A dermoscopic photograph of a skin lesion.
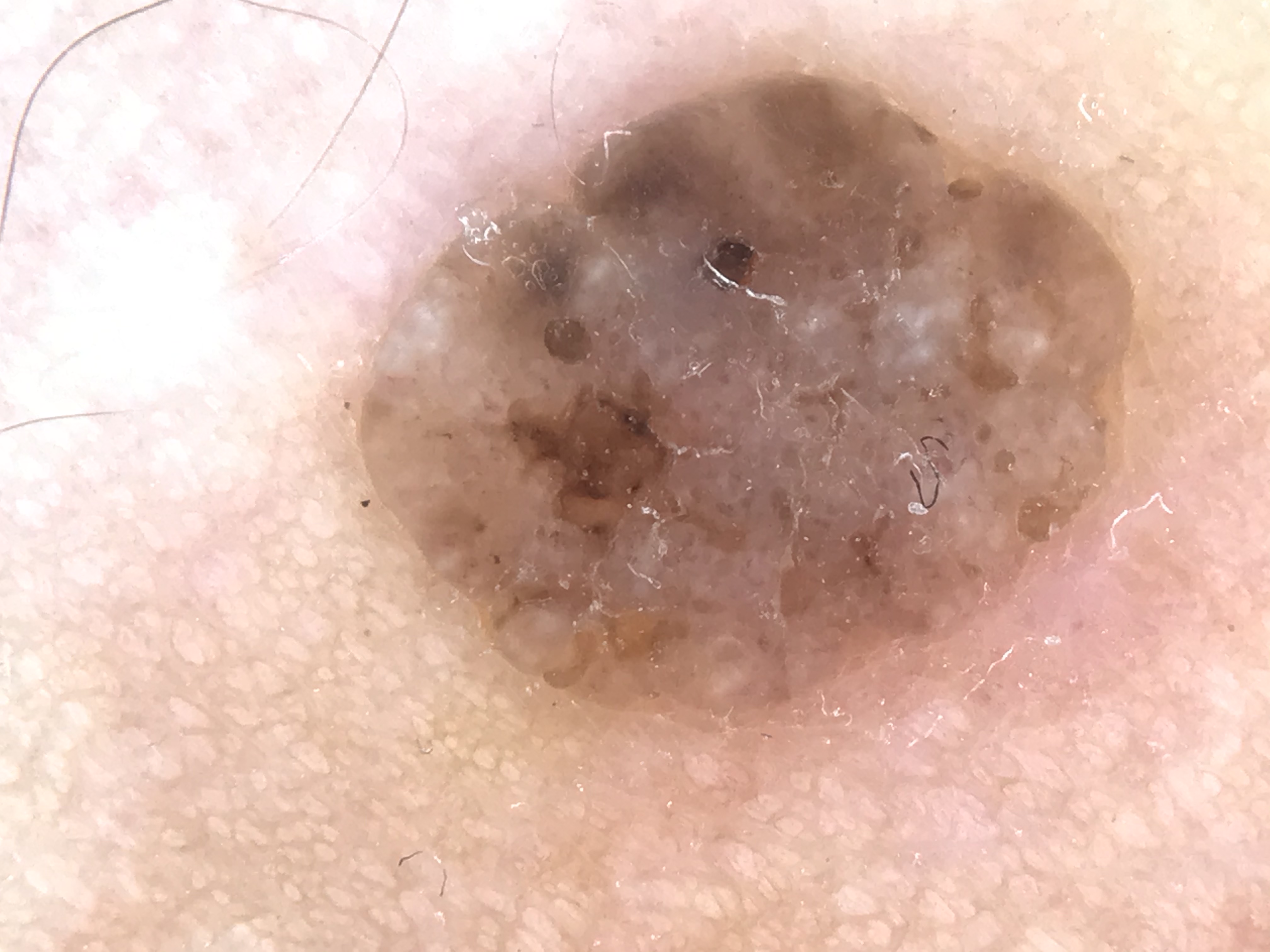The morphology is that of a keratinocytic lesion. Classified as a seborrheic keratosis.